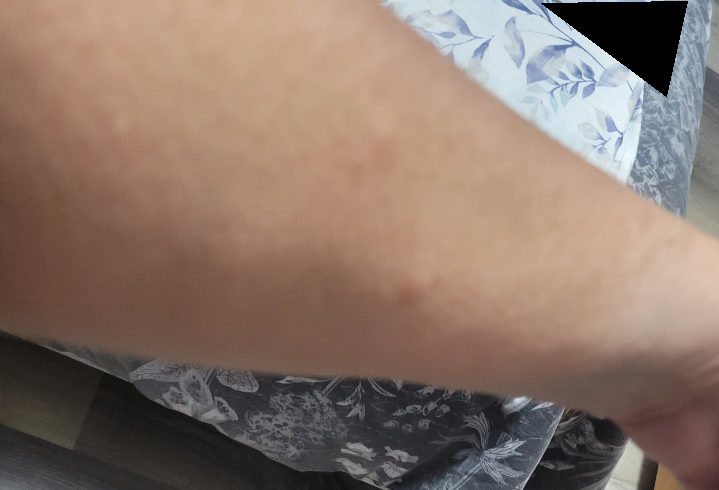<case>
  <assessment>could not be assessed</assessment>
  <shot_type>at a distance</shot_type>
  <symptoms>itching</symptoms>
  <skin_tone>
    <fitzpatrick>III</fitzpatrick>
  </skin_tone>
  <duration>less than one week</duration>
  <body_site>arm</body_site>
</case>